The patient is a female aged 40–49; the photograph is a close-up of the affected area:
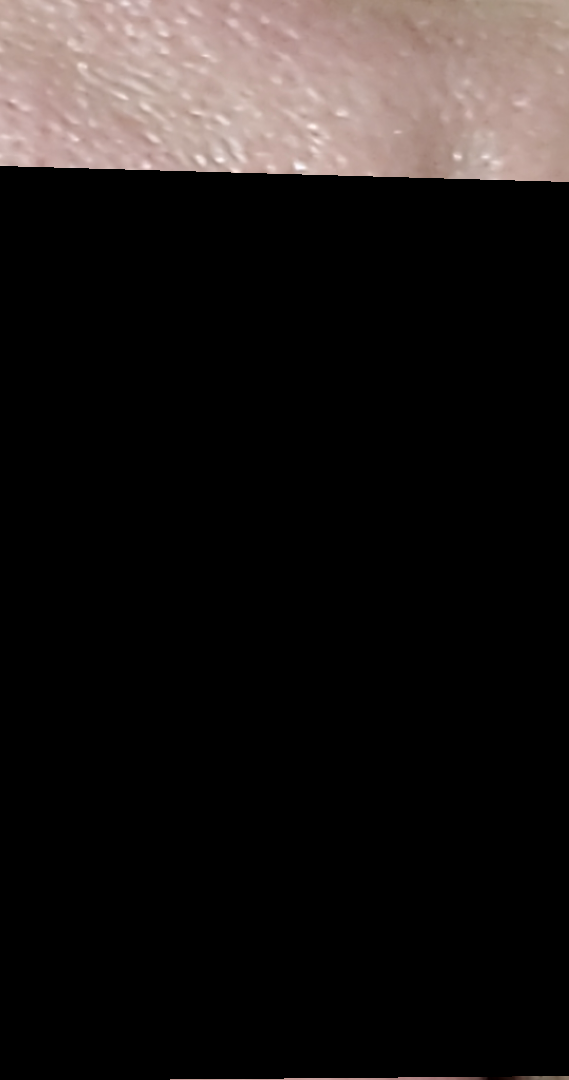Q: What was the assessment?
A: no skin condition identified